A skin lesion imaged with a dermatoscope.
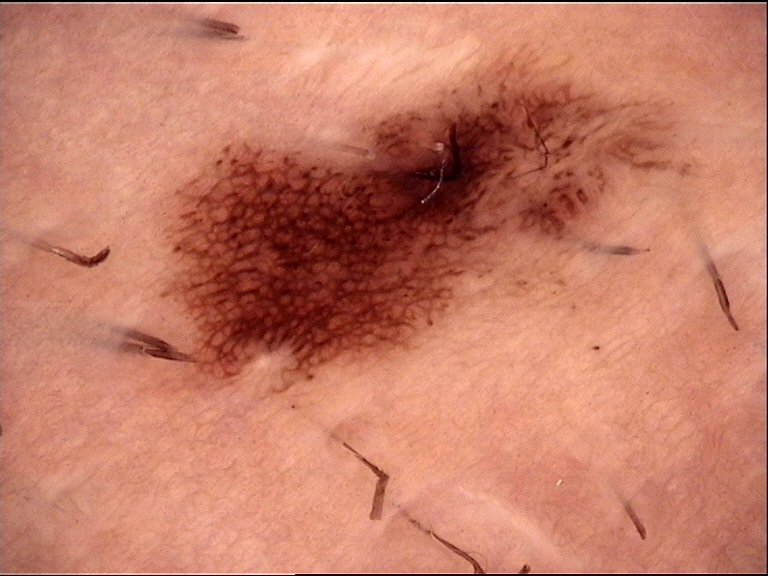Labeled as a benign lesion — a dysplastic junctional nevus.